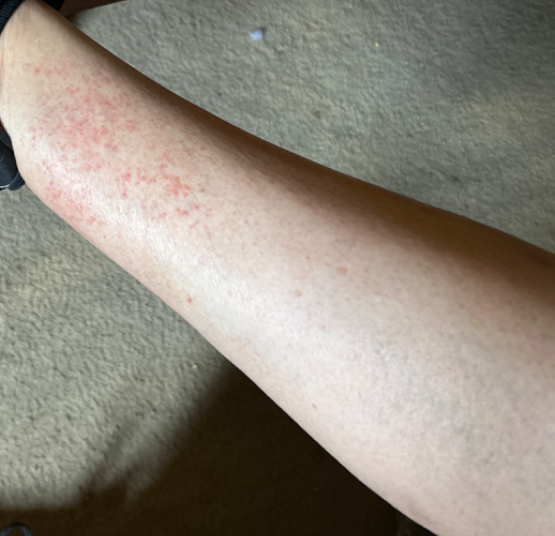Located on the leg.
This image was taken at a distance.
The favored diagnosis is Leukocytoclastic Vasculitis; also consider Pigmented purpuric eruption; also raised was Allergic Contact Dermatitis.